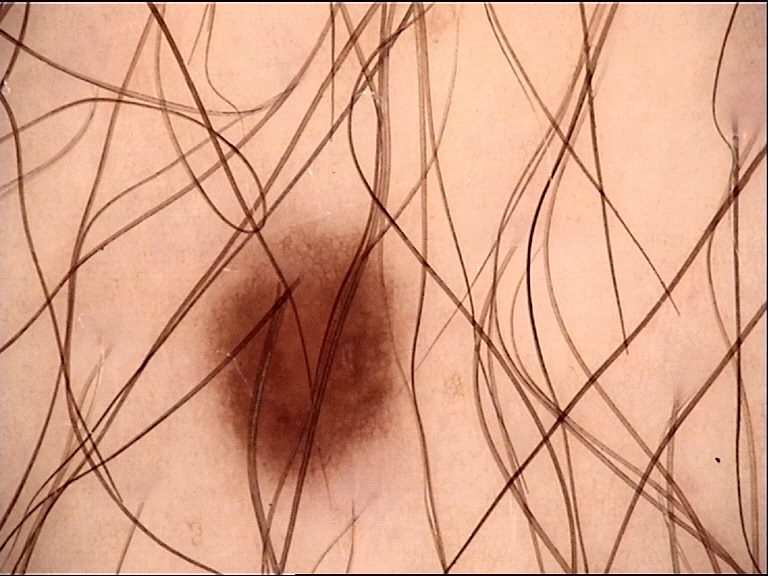diagnostic label = dysplastic junctional nevus (expert consensus).